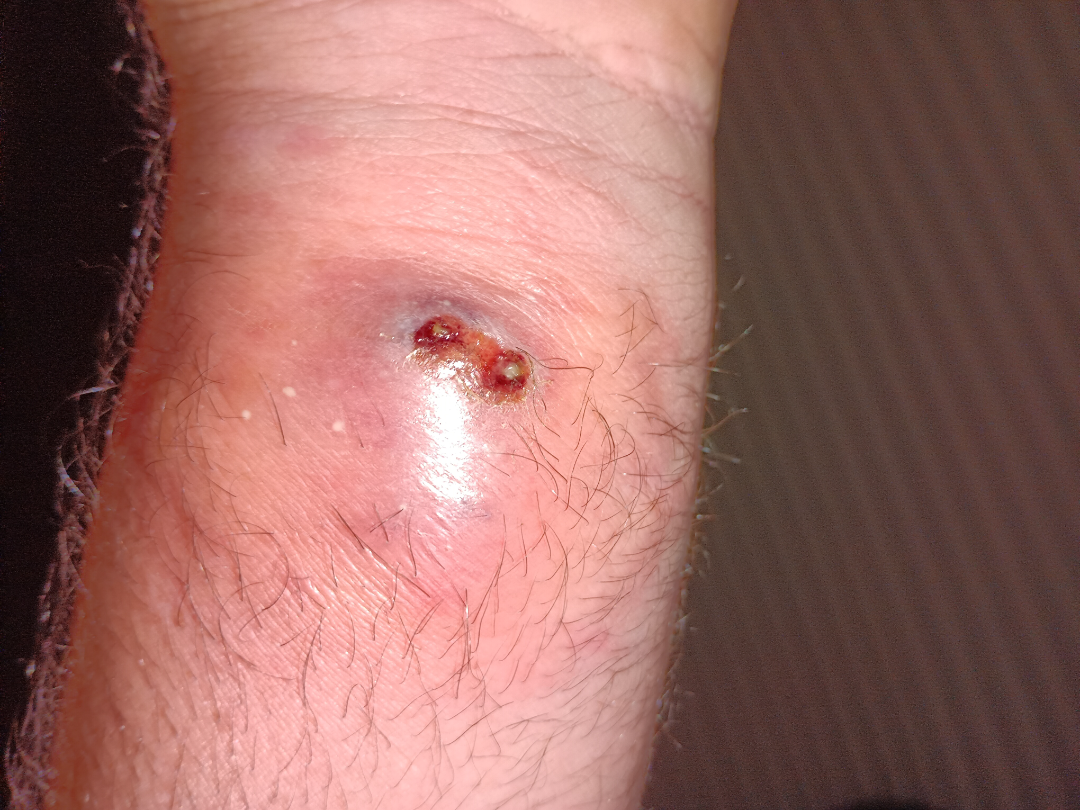The patient notes the condition has been present for one to four weeks. The arm is involved. Close-up view. Self-categorized by the patient as a rash. Reported lesion symptoms include darkening, burning, itching, pain, enlargement and bleeding. The patient notes the lesion is raised or bumpy and fluid-filled. The contributor is a male aged 40–49. Associated systemic symptoms include chills, joint pain and fever. Fitzpatrick phototype III. Abscess (favored); Insect Bite (remote); Sweet syndrome (remote); Pyoderma Gangrenosum (remote); Skin and soft tissue atypical mycobacterial infection (remote); Snake bite - wound (remote).